Male patient, age 18–29 · reported lesion symptoms include itching · the back of the hand is involved · the condition has been present for about one day · the patient described the issue as a rash · the contributor notes the lesion is fluid-filled and raised or bumpy · the photograph was taken at a distance: 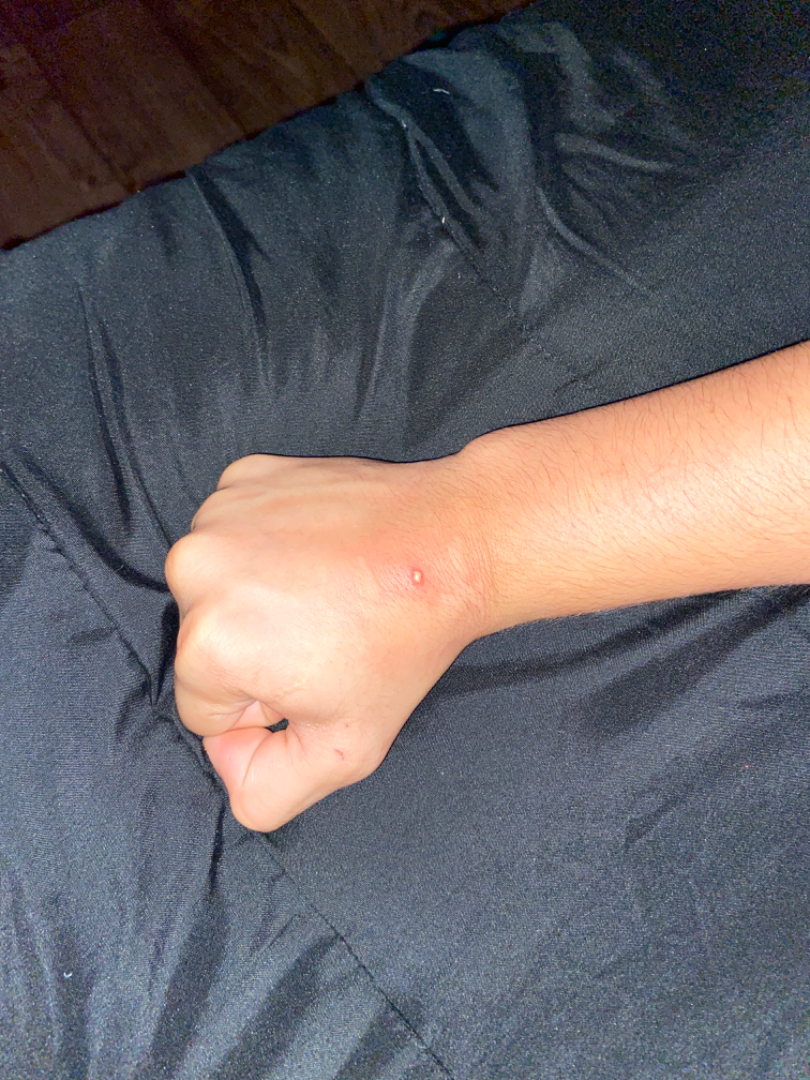differential: the impression was split between Cellulitis and Insect Bite; with consideration of Abscess; less probable is pustules